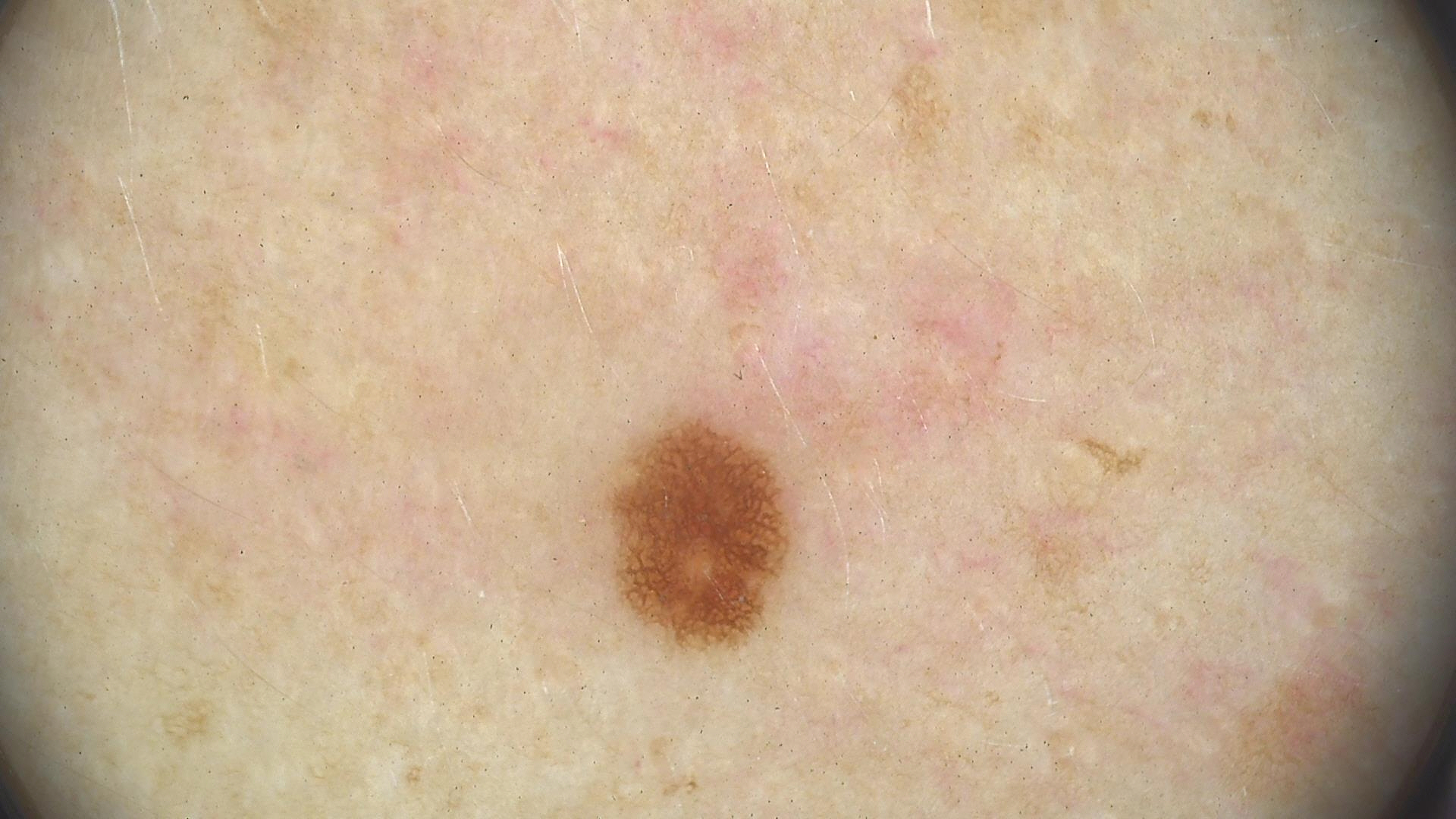– image type · dermatoscopy
– diagnostic label · junctional nevus (expert consensus)